A dermatoscopic image of a skin lesion: 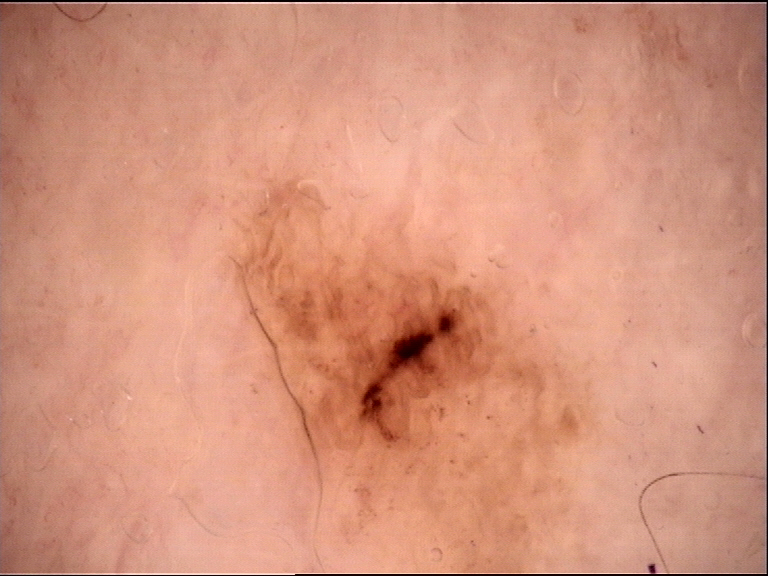  diagnosis:
    name: dysplastic junctional nevus
    code: jd
    malignancy: benign
    super_class: melanocytic
    confirmation: expert consensus